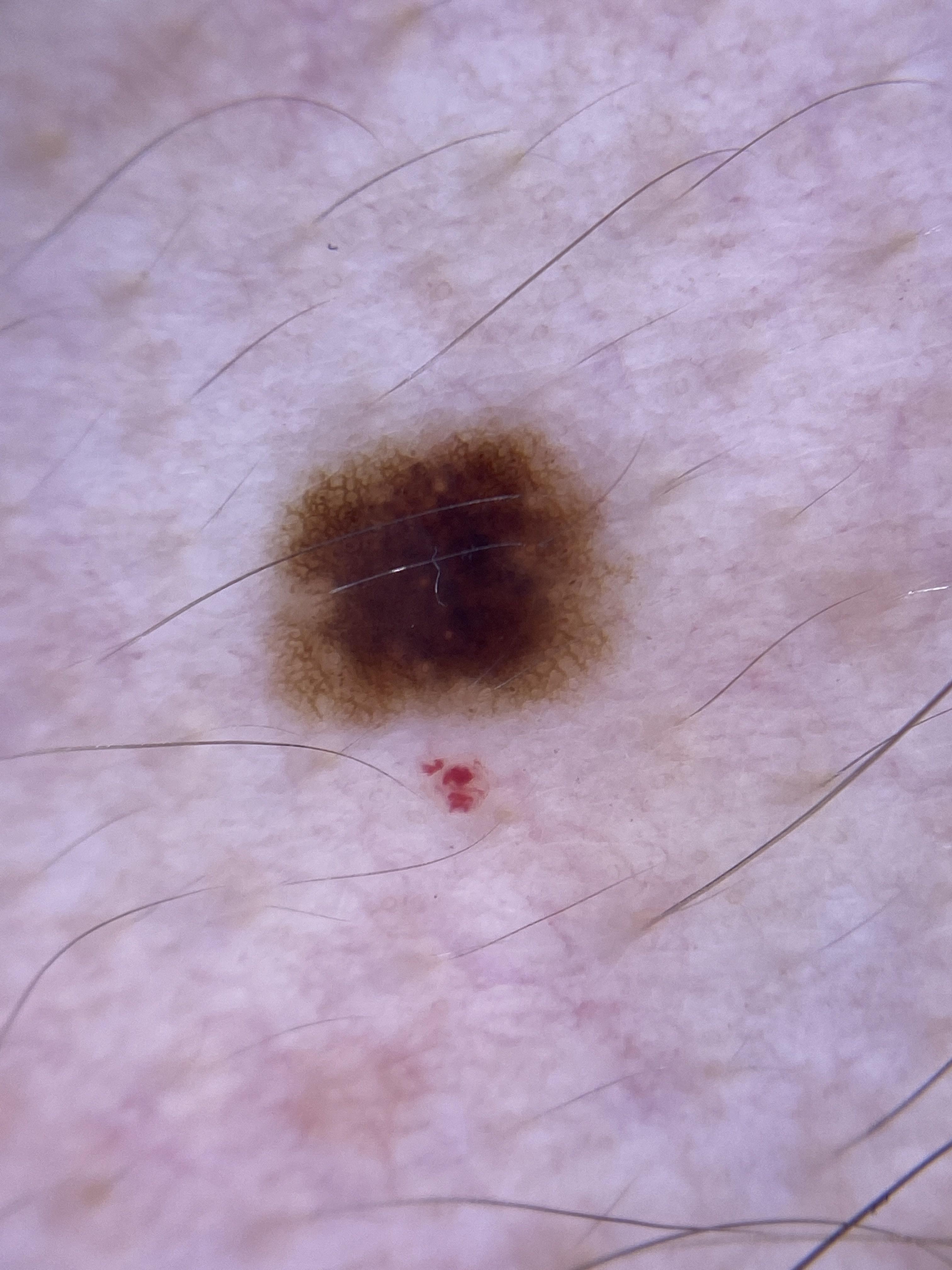A dermoscopic image of a skin lesion. Per the chart, melanoma in a first-degree relative. Fitzpatrick II. A male subject aged approximately 20. The lesion involves the trunk. Expert review favored a melanocytic lesion — a nevus.